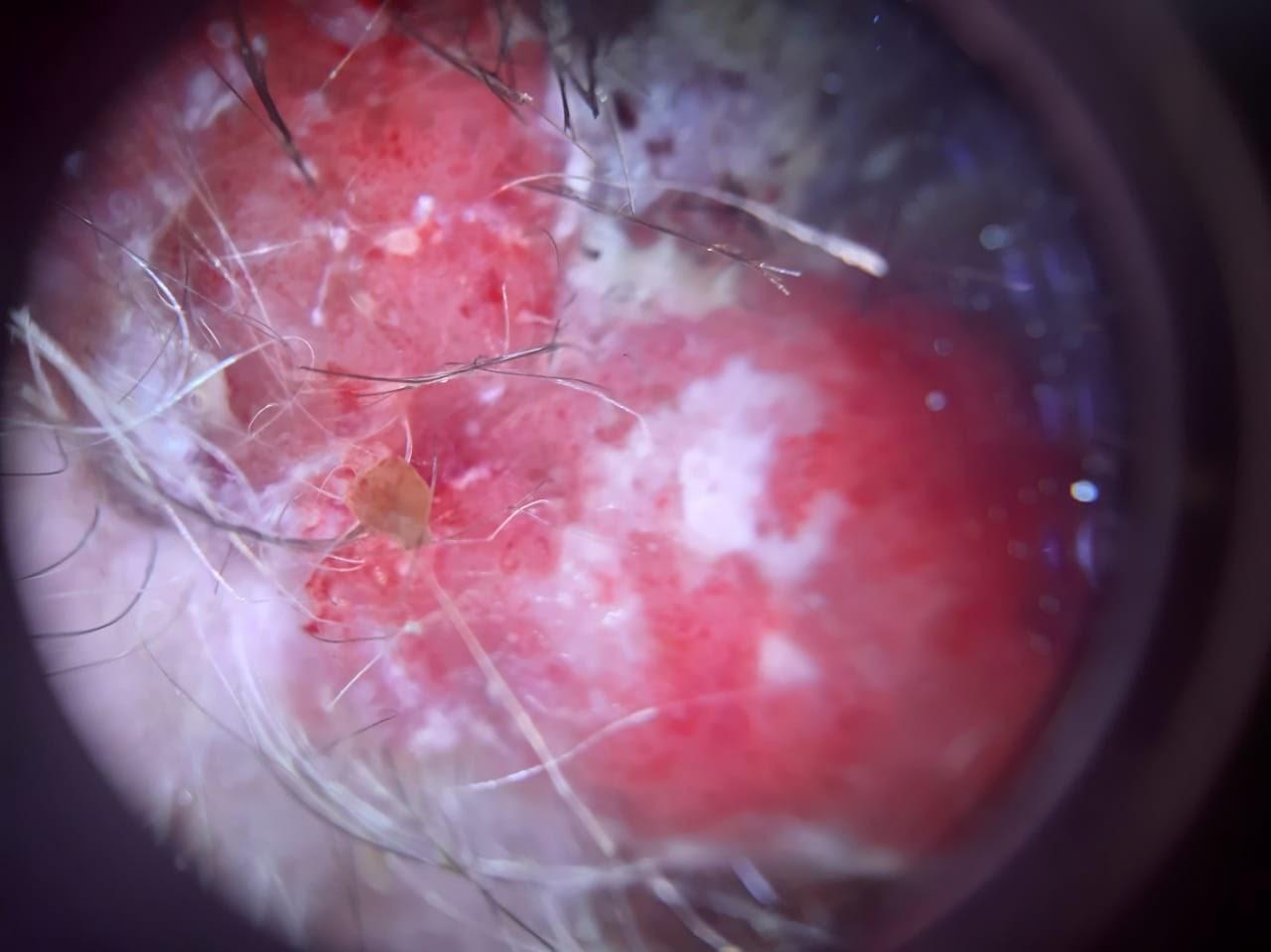| key | value |
|---|---|
| modality | dermatoscopic image |
| skin type | II |
| subject | female, approximately 85 years of age or older |
| body site | the head or neck |
| pathology | Melanoma (biopsy-proven) |